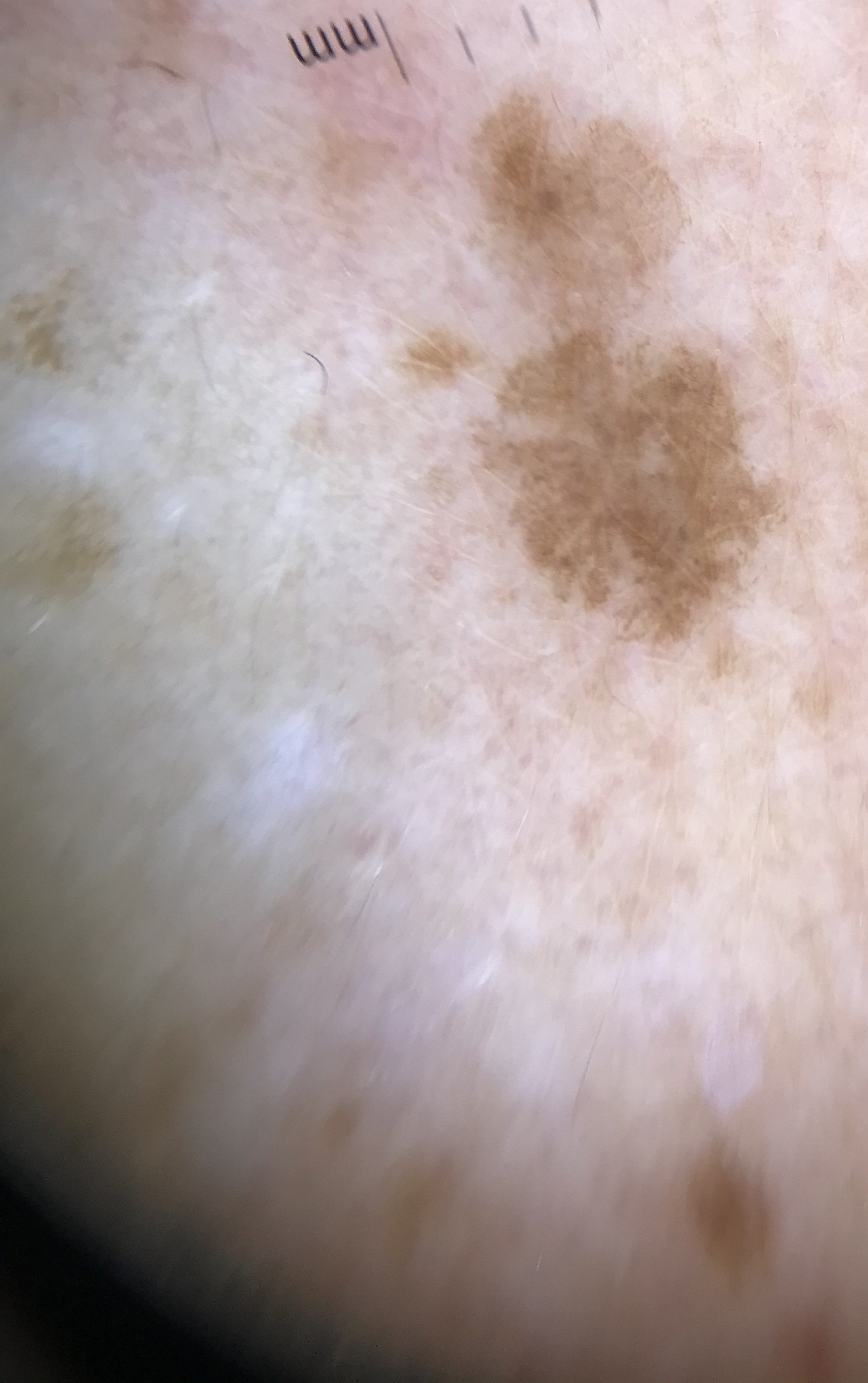Conclusion:
Consistent with a solar lentigo.